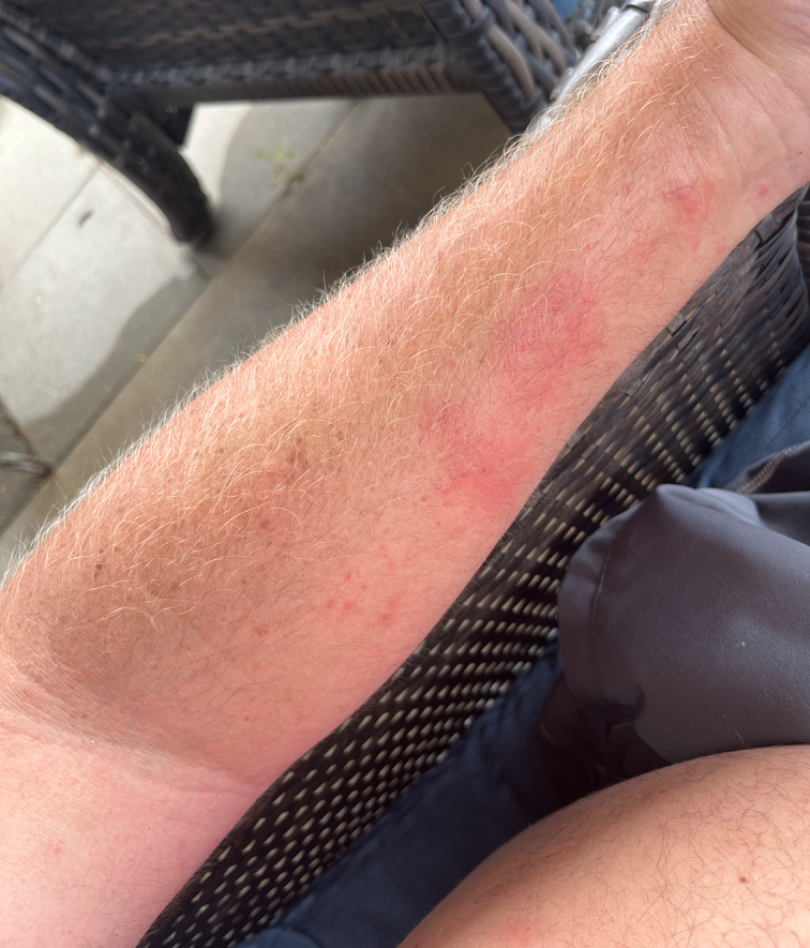The image was not sufficient for the reviewer to characterize the skin condition.
The patient reports the lesion is raised or bumpy and fluid-filled.
The patient considered this a rash.
This image was taken at an angle.
The patient reports the condition has been present for less than one week.
The affected area is the front of the torso and arm.
No constitutional symptoms were reported.
The patient is 50–59, male.